The photograph is a close-up of the affected area — 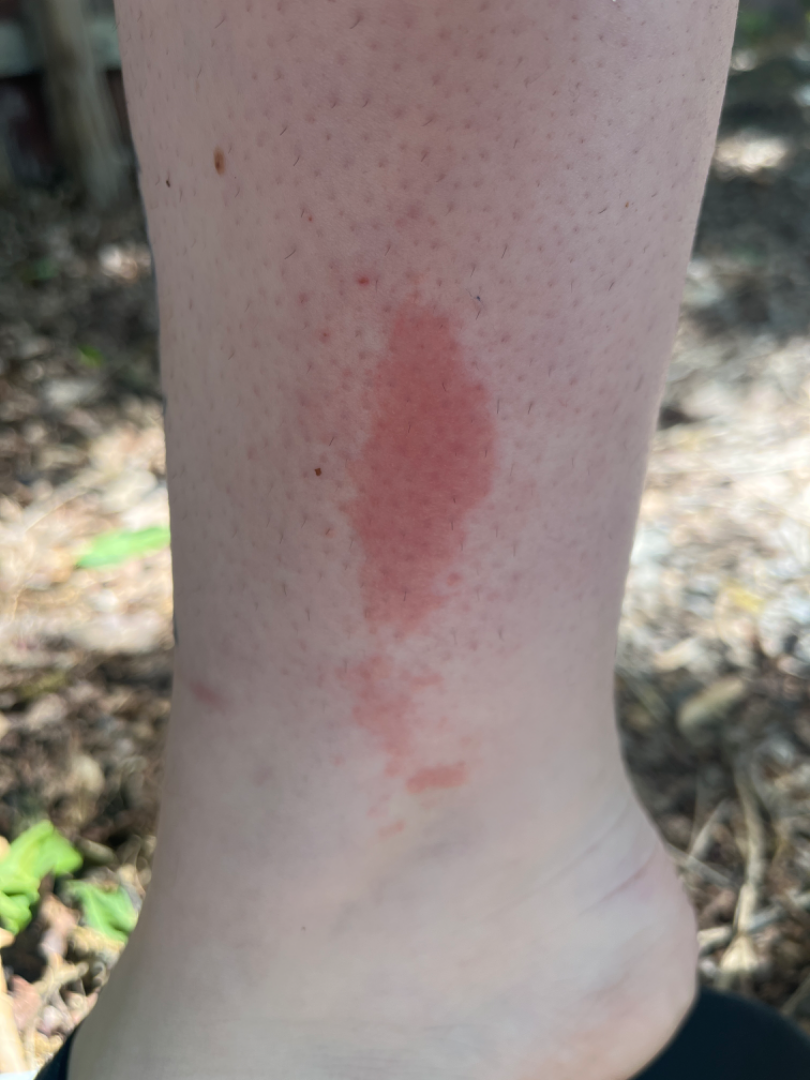The differential includes Allergic Contact Dermatitis and Irritant Contact Dermatitis, with no clear leading consideration.